Texture is reported as flat; self-categorized by the patient as a rash; a close-up photograph; the lesion involves the leg; the contributor is 18–29, female; reported duration is less than one week; reported lesion symptoms include enlargement:
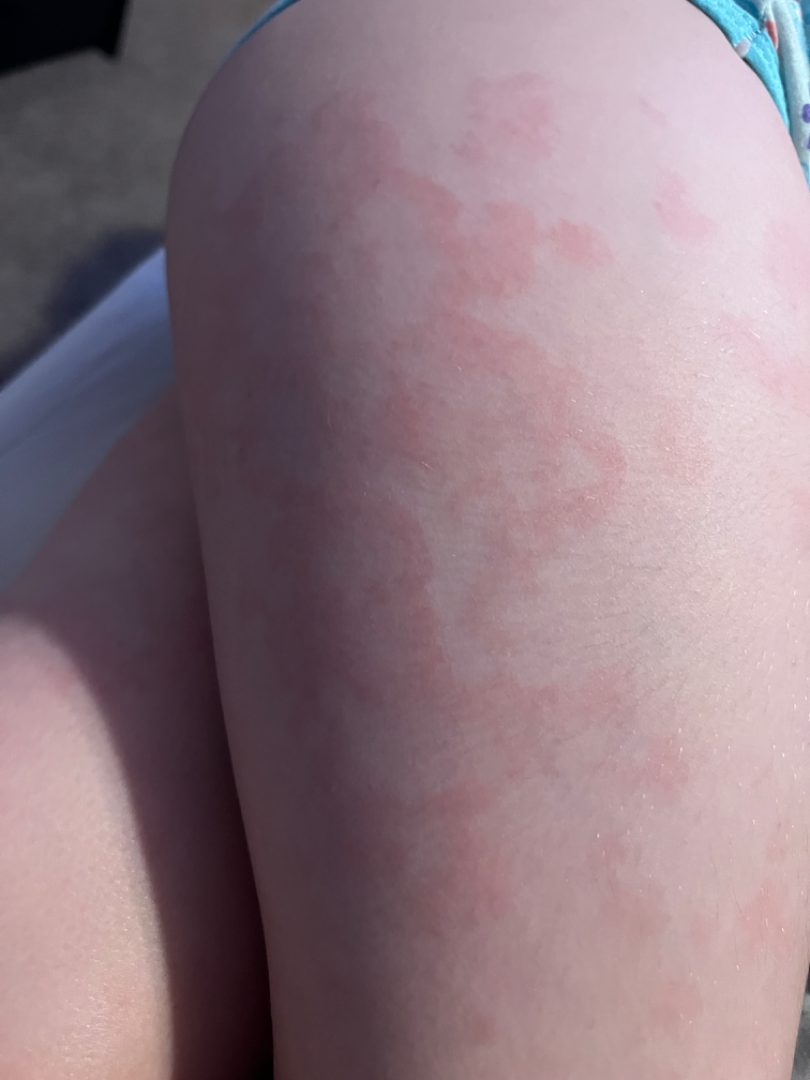Q: What is the dermatologist's impression?
A: Drug Rash (considered); Urticaria (considered); Erythema marginatum (considered)